A dermoscopic image of a skin lesion · a male patient aged 68 to 72: 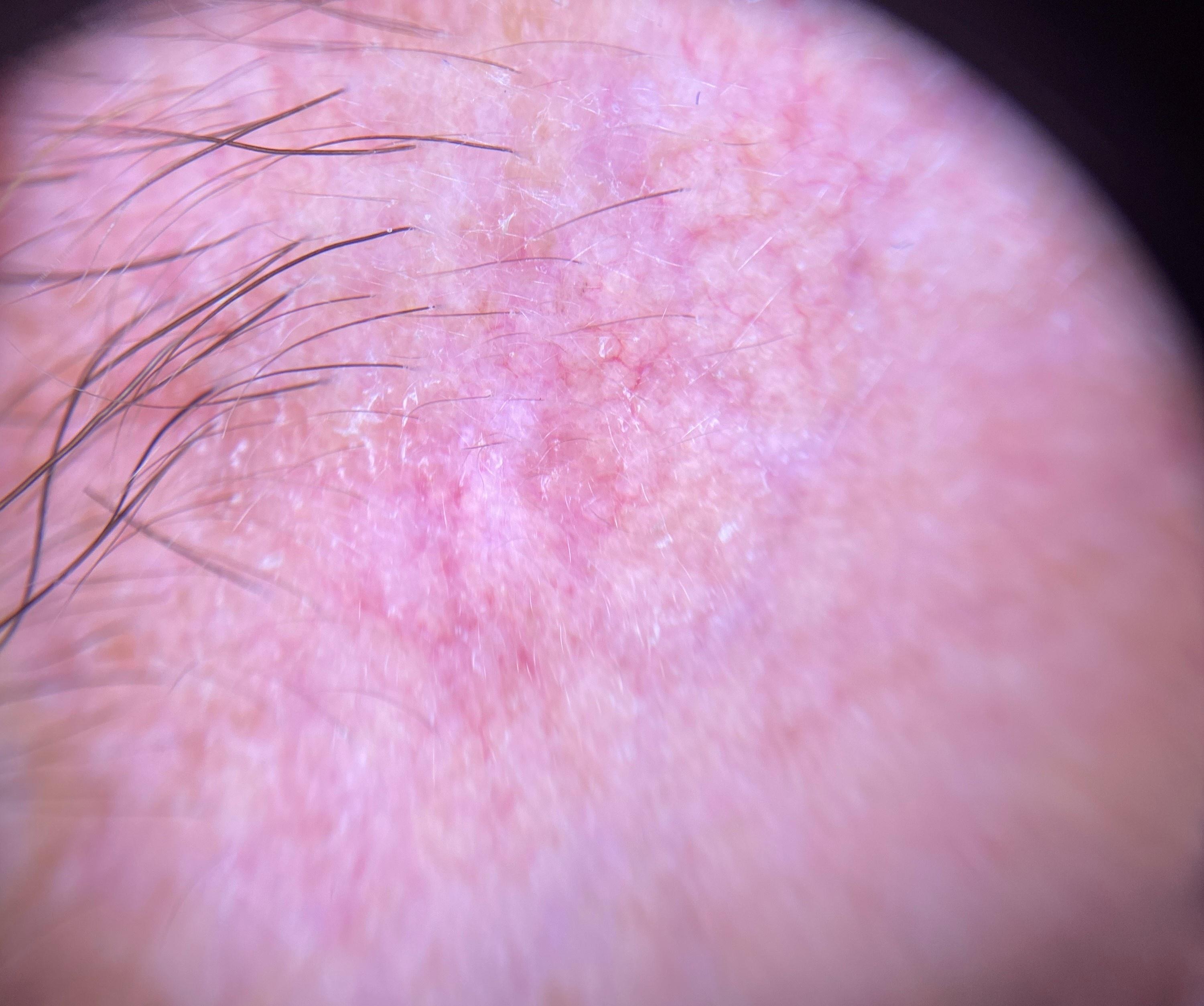The lesion is located on the head or neck. Biopsy-confirmed as an epidermal lesion — a squamous cell carcinoma.